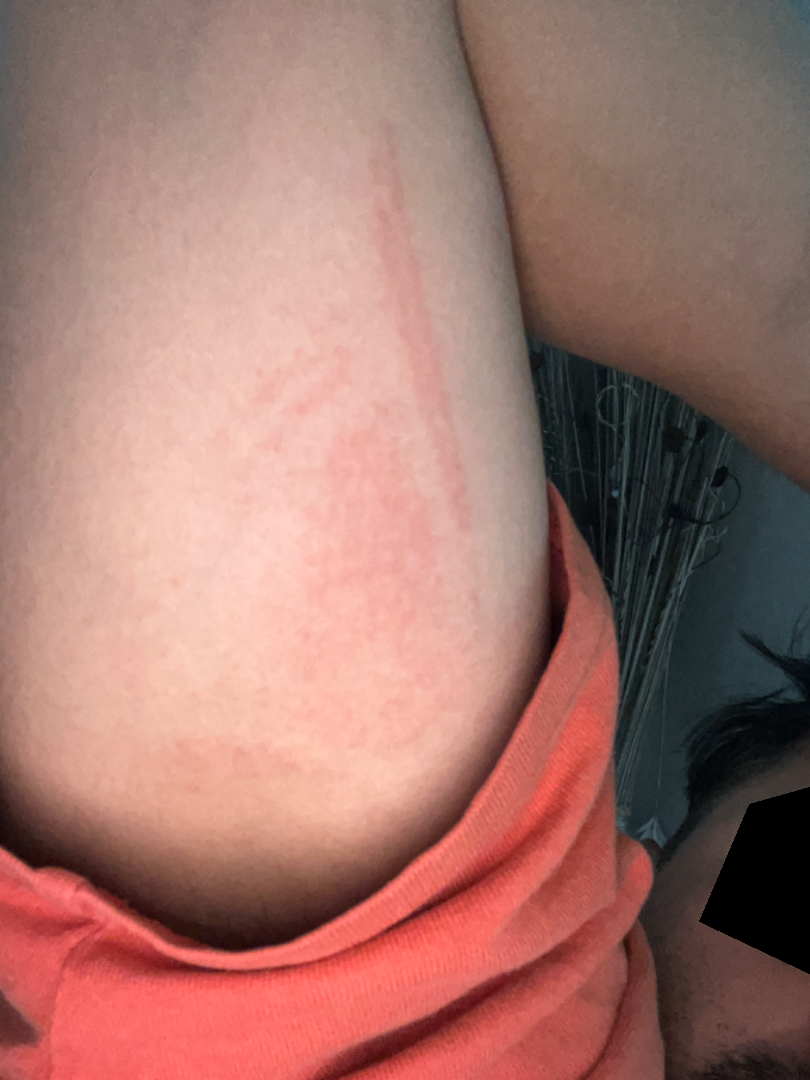The patient reports the lesion is raised or bumpy. Located on the arm. Skin tone: Fitzpatrick phototype II; lay reviewers estimated MST 3 (US pool) or 2 (India pool). Present for less than one week. Male contributor, age 30–39. No constitutional symptoms were reported. This is a close-up image. On photographic review by a dermatologist: the favored diagnosis is Urticaria; an alternative is Eczema; also raised was Allergic Contact Dermatitis.